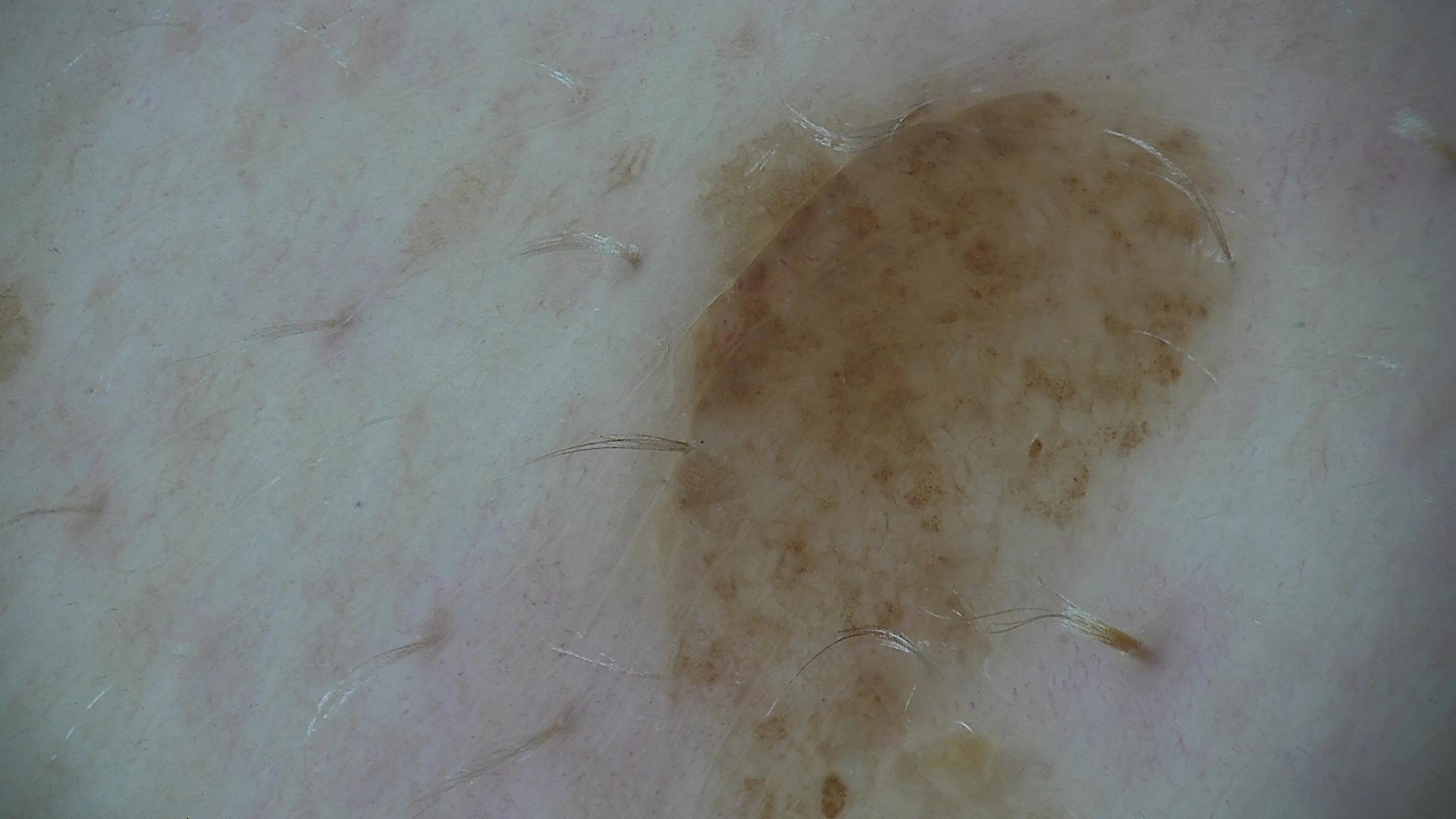Classified as a compound nevus.